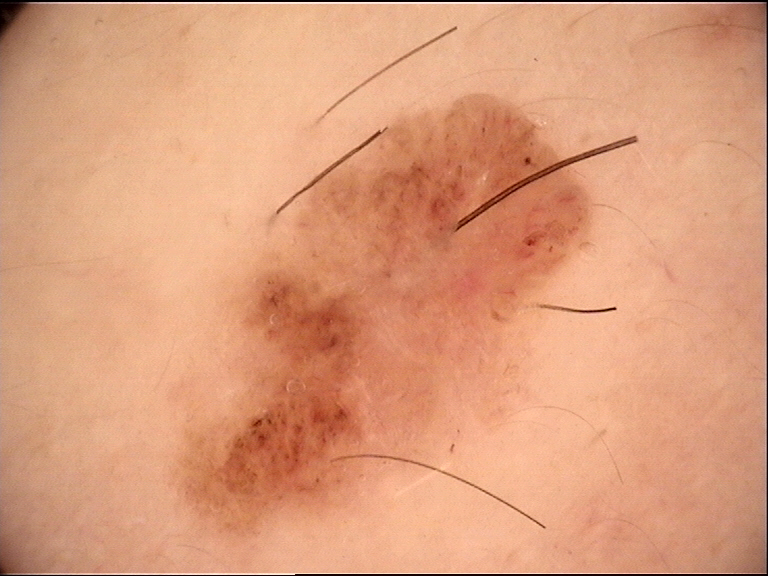diagnosis = compound nevus (expert consensus).